The affected area is the palm · the patient considered this skin that appeared healthy to them · self-reported Fitzpatrick skin type IV · the photo was captured at a distance · the contributor is male:
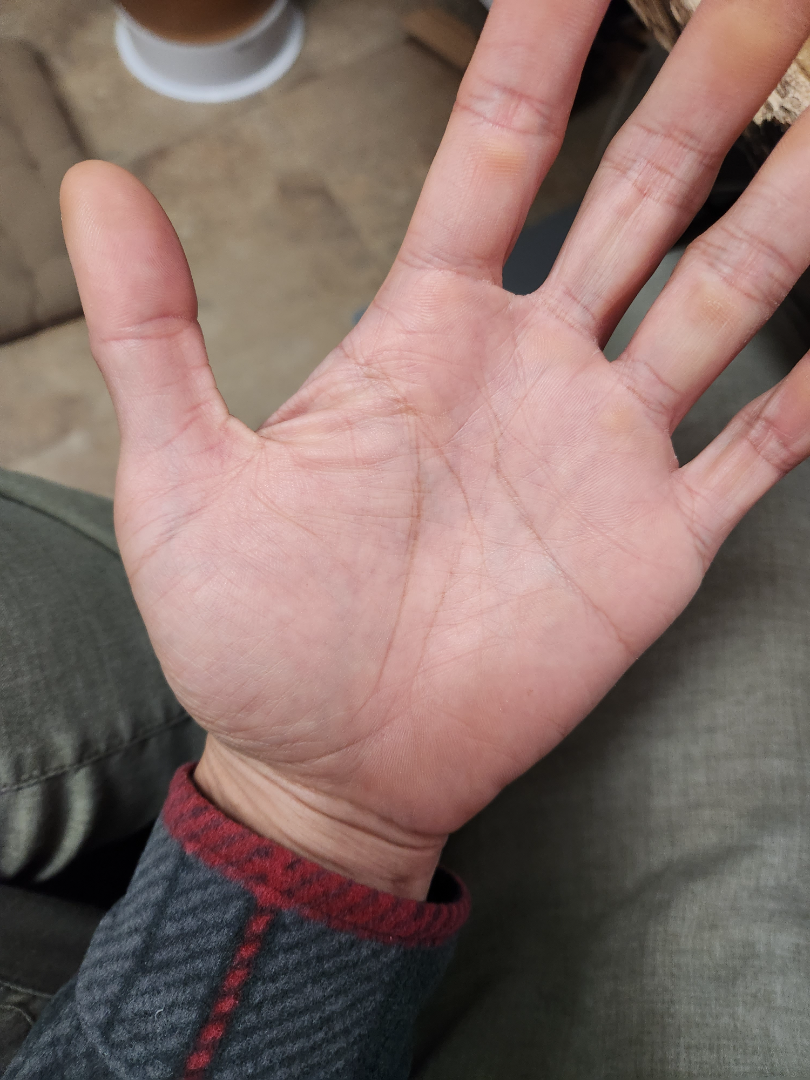Findings:
Hyperlinear palm and Eczema were considered with similar weight.